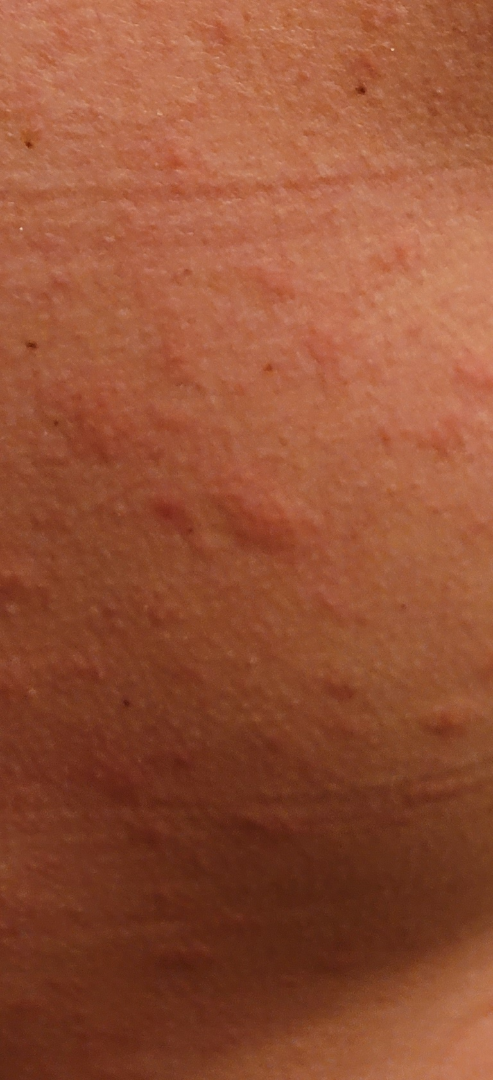Most consistent with Urticaria.